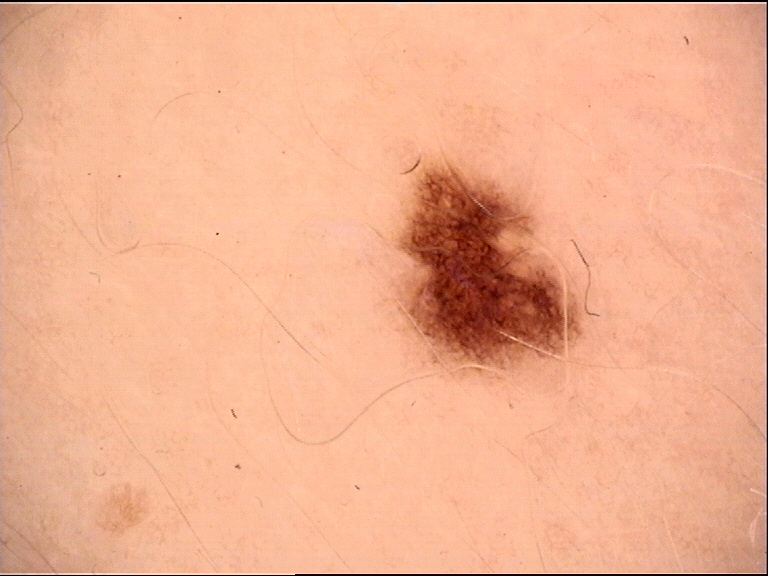The diagnostic label was a dysplastic junctional nevus.